A skin lesion imaged with a dermatoscope; a male patient 72 years old; acquired for a research image collection, with no referral diagnosis.
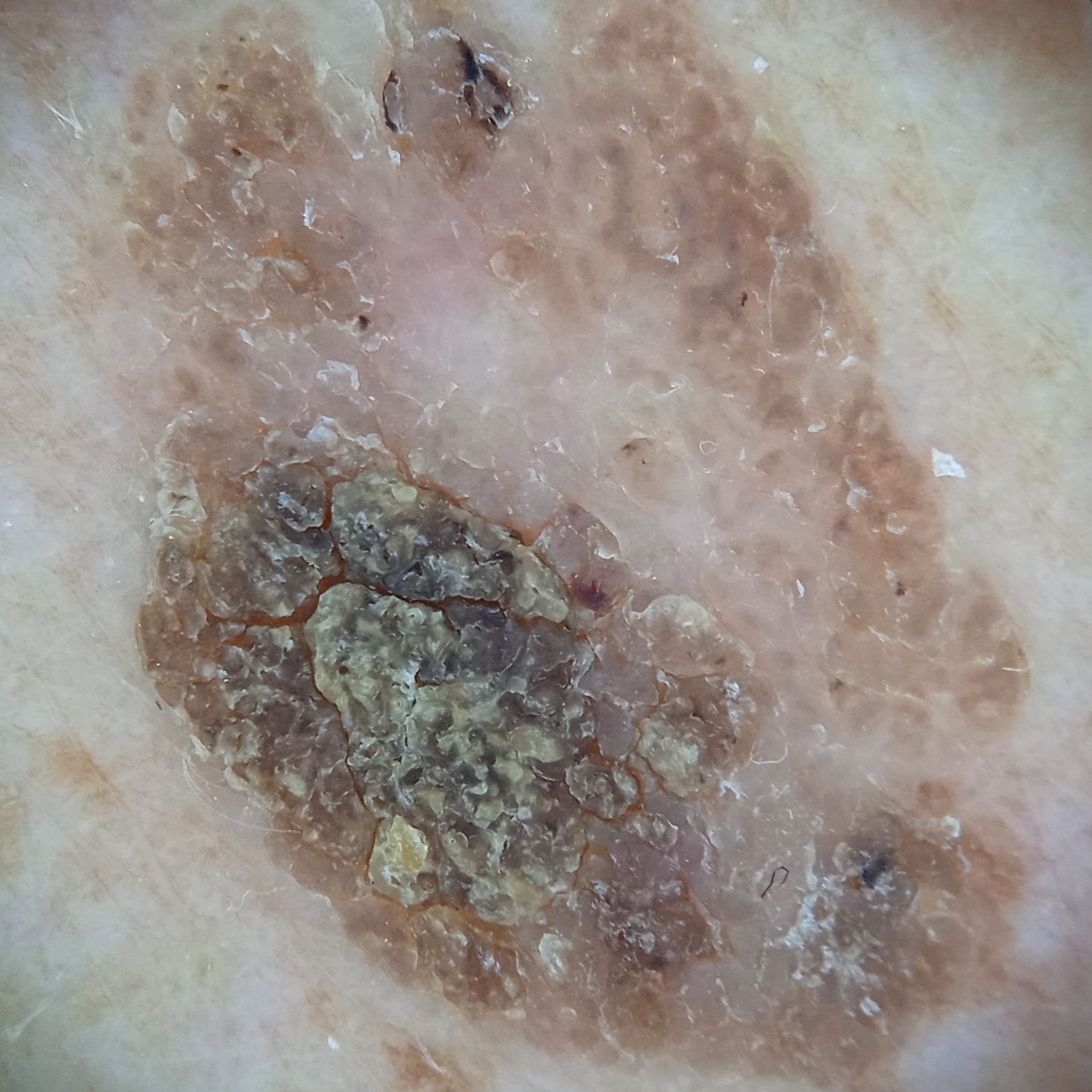| field | value |
|---|---|
| anatomic site | the back |
| diameter | 13.7 mm |
| assessment | seborrheic keratosis (dermatologist consensus) |